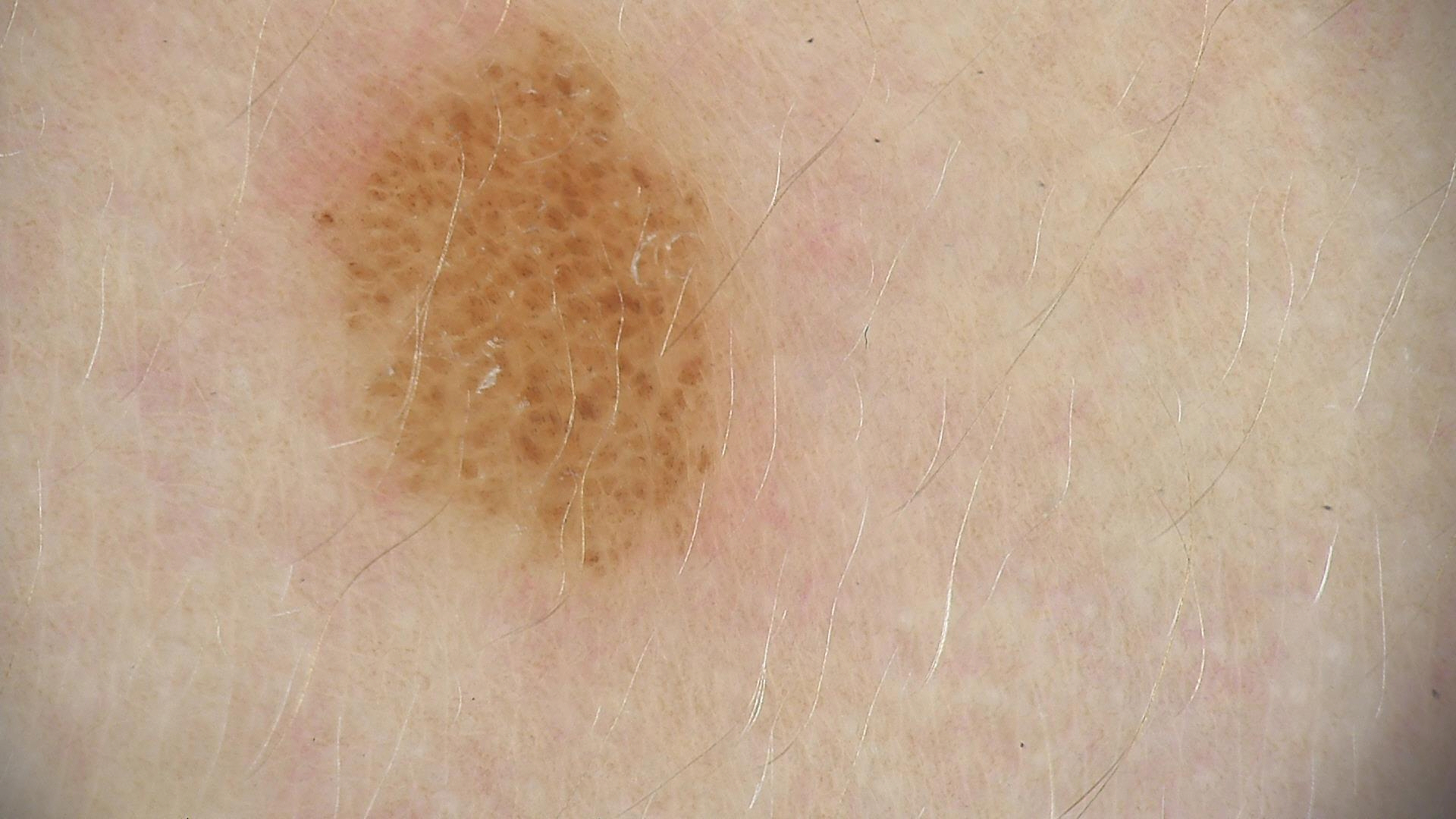The diagnostic label was a compound nevus.